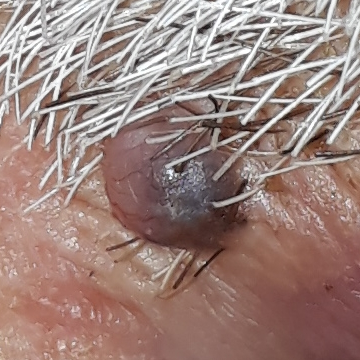The lesion is on a lip. The biopsy diagnosis was a basal cell carcinoma.